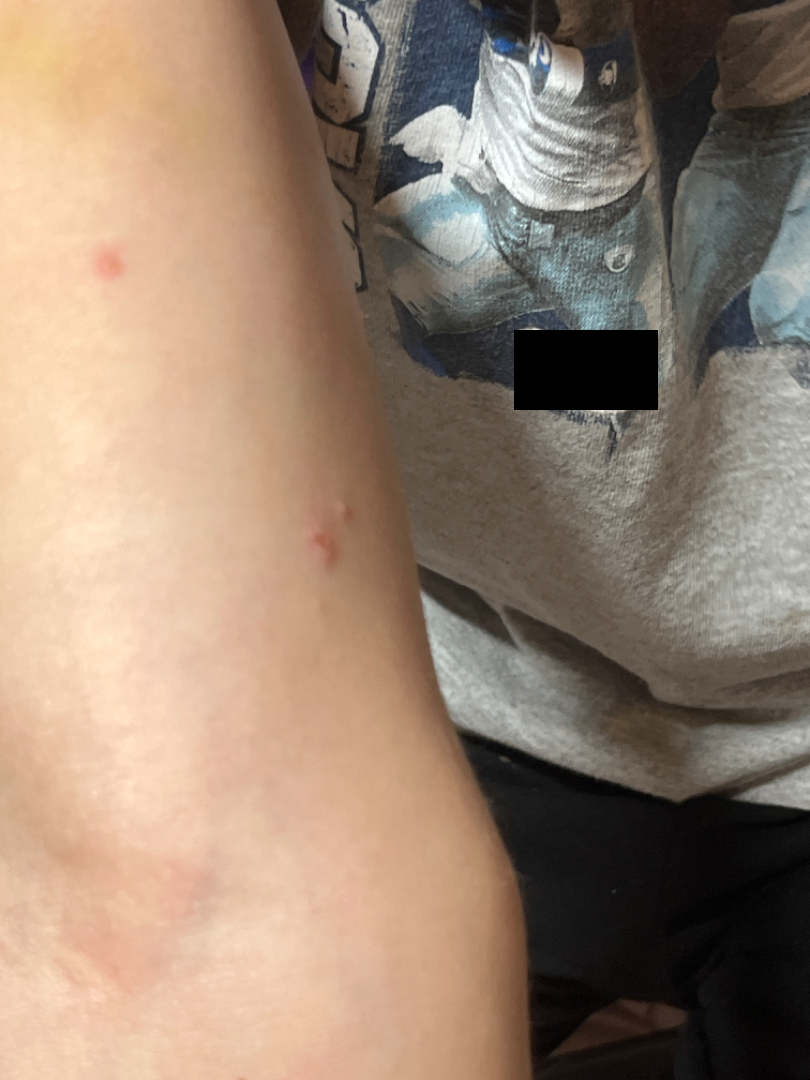| key | value |
|---|---|
| view | at an angle |
| affected area | head or neck and arm |
| impression | reviewed remotely by one dermatologist: in keeping with Psoriasis |